A female subject in their early 50s · a clinical photo of a skin lesion taken with a smartphone · the patient is Fitzpatrick III · by history, prior malignancy (patient or family).
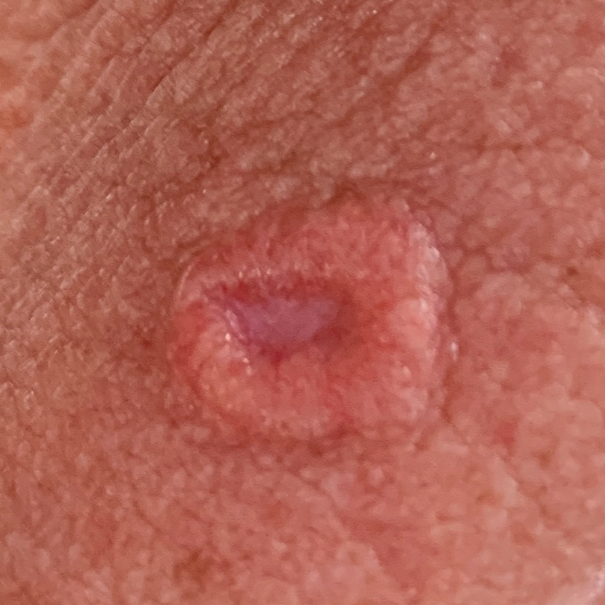Findings: The lesion was found on the neck. The lesion measures 18 × 10 mm. Diagnosis: Biopsy-confirmed as a basal cell carcinoma.